Reported lesion symptoms include enlargement, pain, itching and bothersome appearance · the contributor is 18–29, female · the patient described the issue as a rash · a close-up photograph · the condition has been present for one to four weeks · the back of the hand, arm and head or neck are involved — 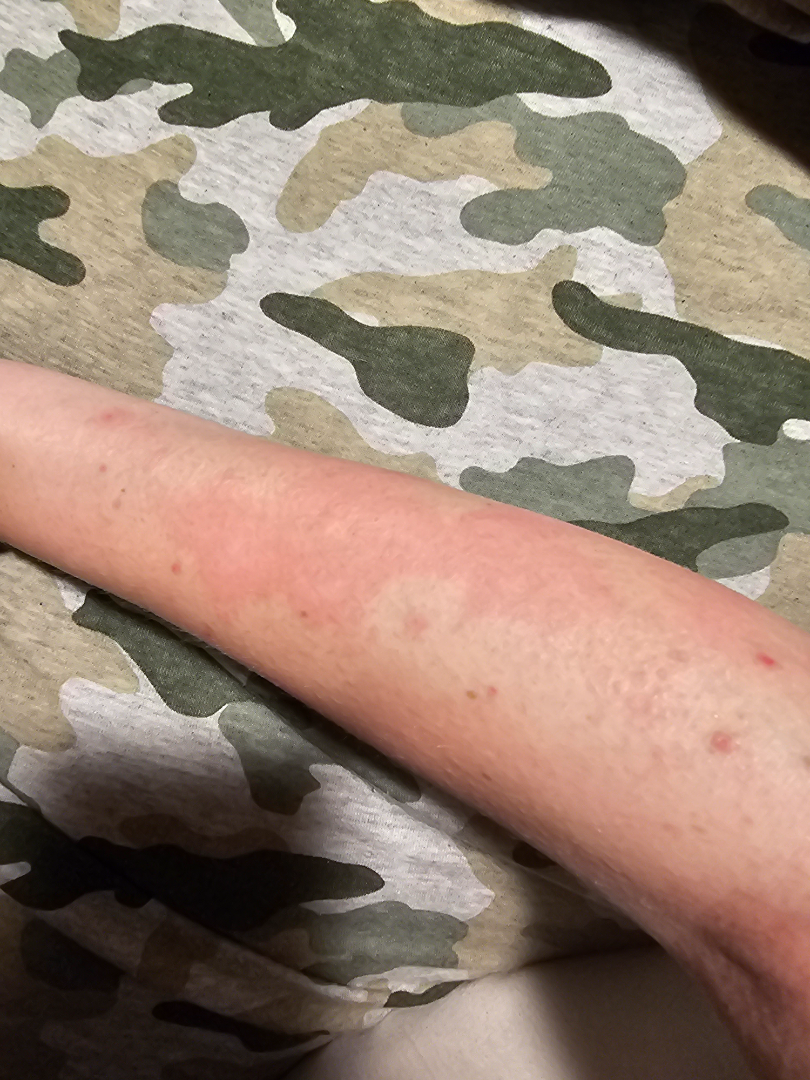The leading consideration is Hypersensitivity; also consider Irritant Contact Dermatitis.